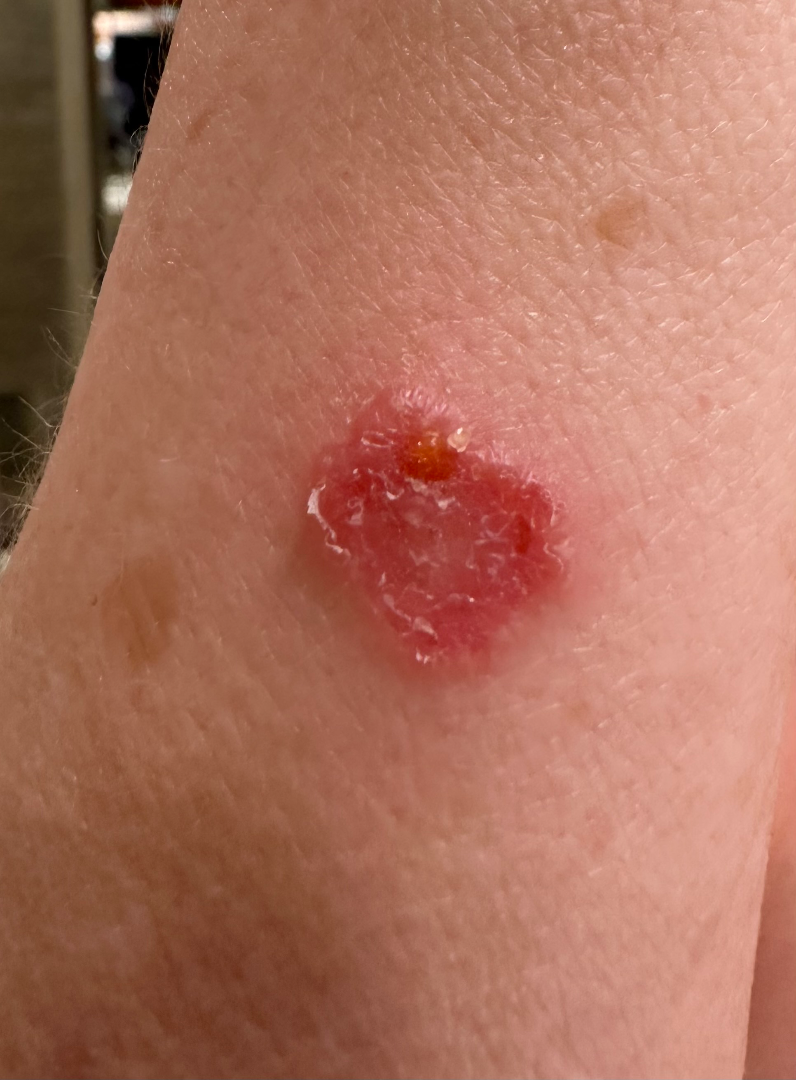  patient_category: a rash
  body_site: arm
  duration: less than one week
  texture:
    - rough or flaky
    - raised or bumpy
  symptoms: itching
  skin_tone:
    fitzpatrick: I
  shot_type: close-up
  systemic_symptoms: mouth sores
  differential:
    leading:
      - Impetigo